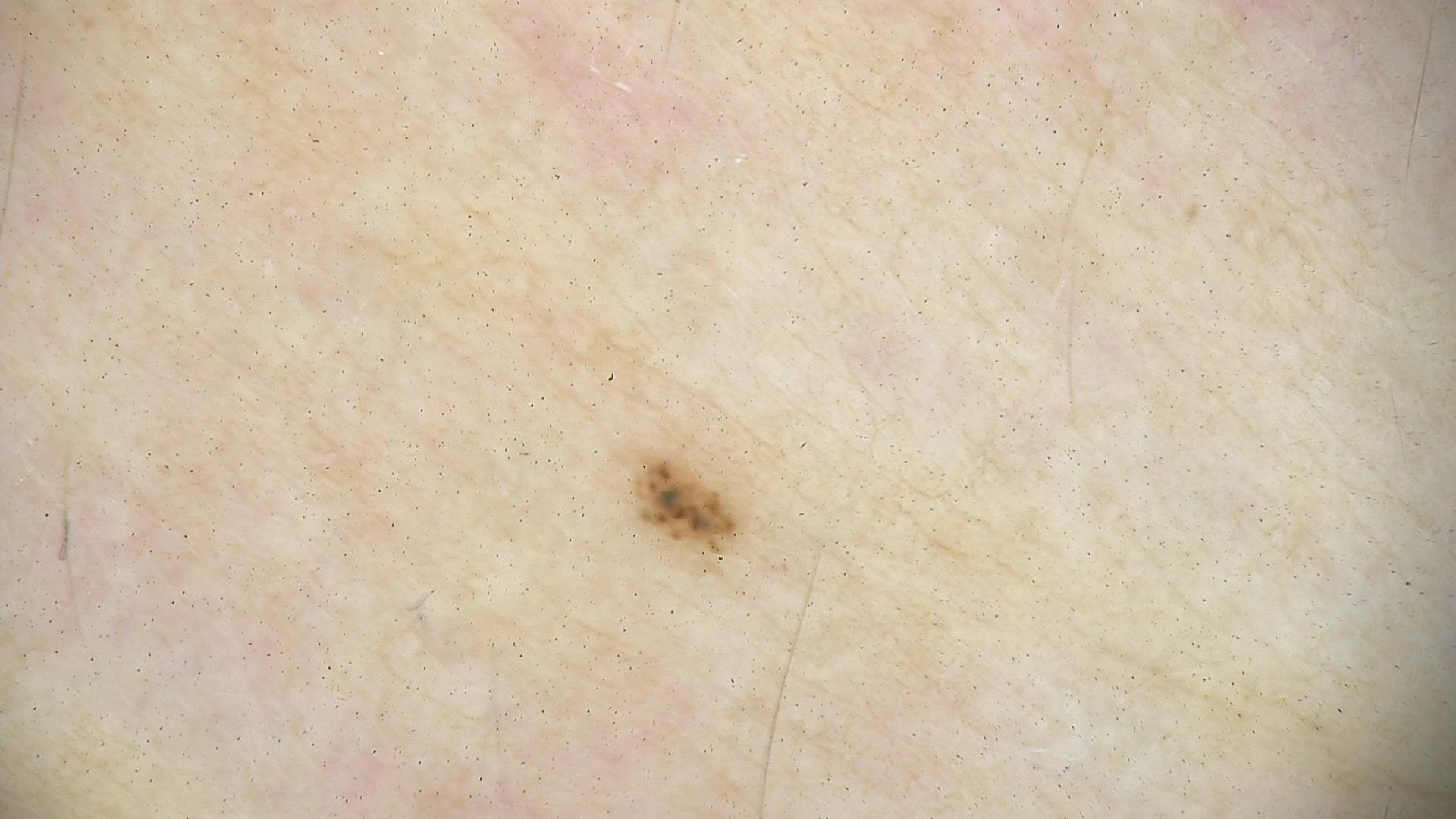- diagnostic label · dysplastic junctional nevus (expert consensus)